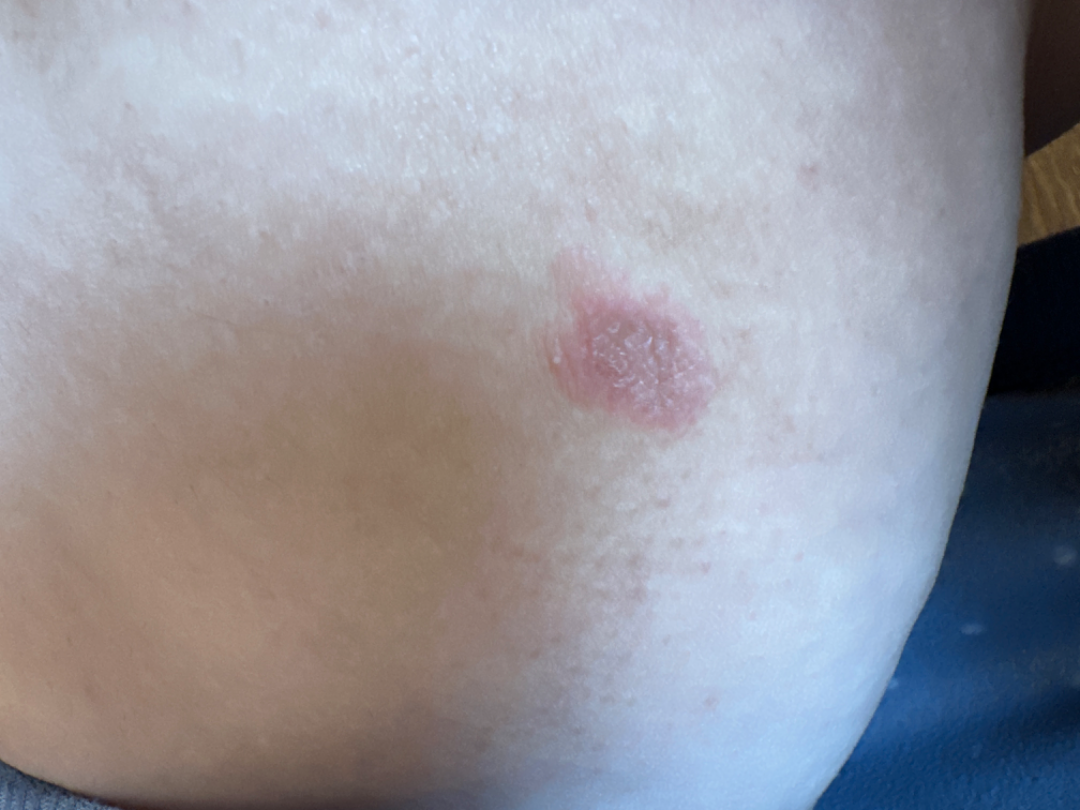Review: The reviewer was unable to grade this case for skin condition. Patient information: The photo was captured at an angle.